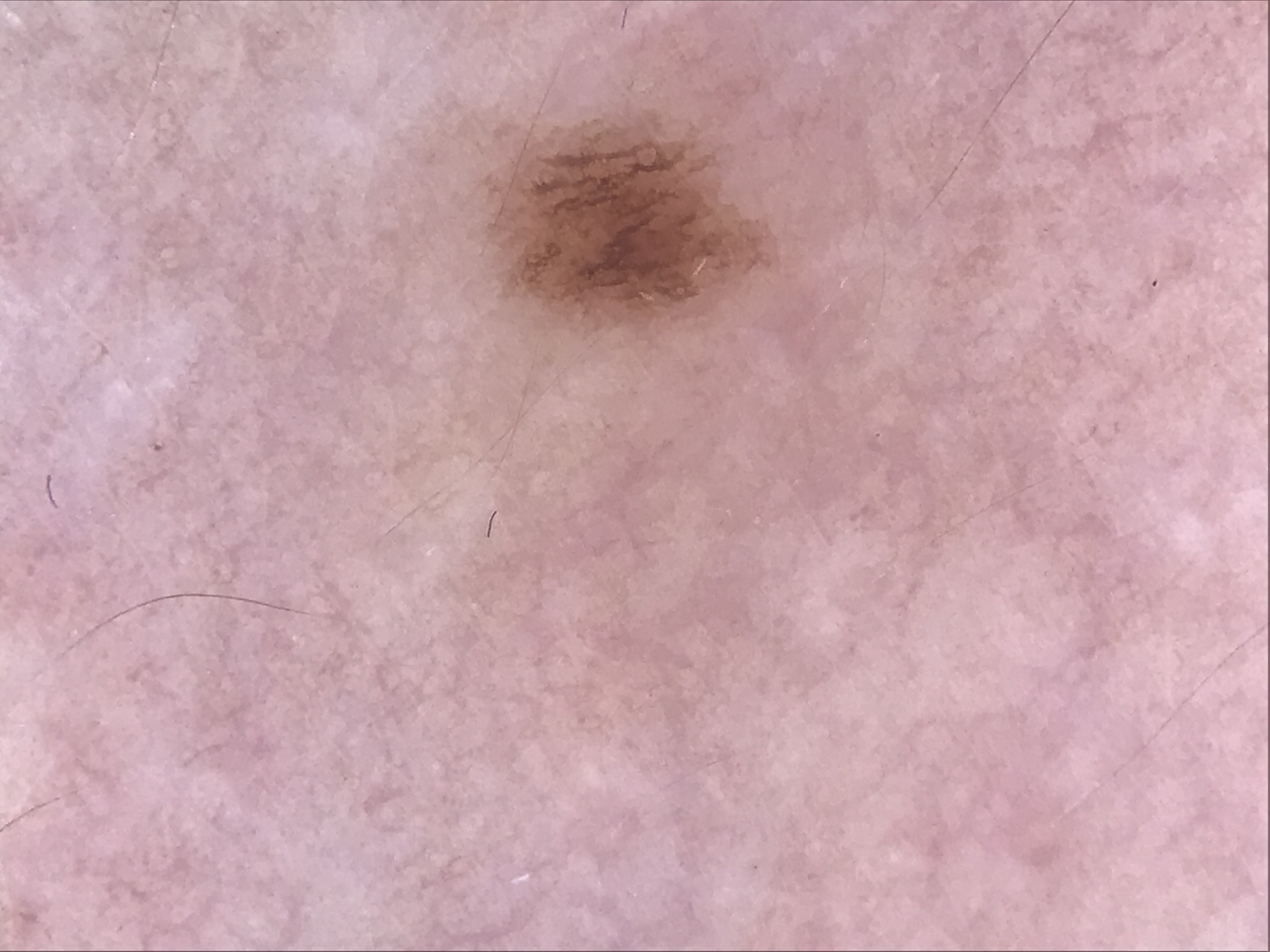Case:
• class: dysplastic junctional nevus (expert consensus)